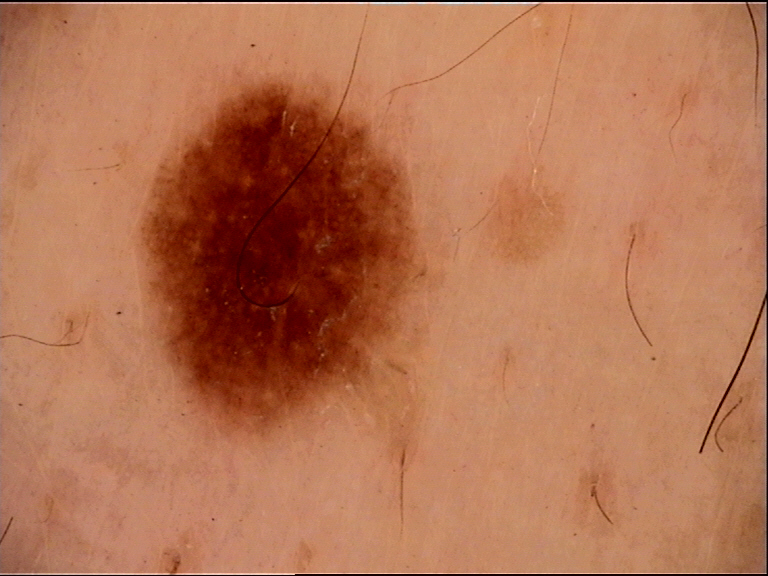The diagnosis was a dysplastic junctional nevus.